A dermoscopic image of a skin lesion.
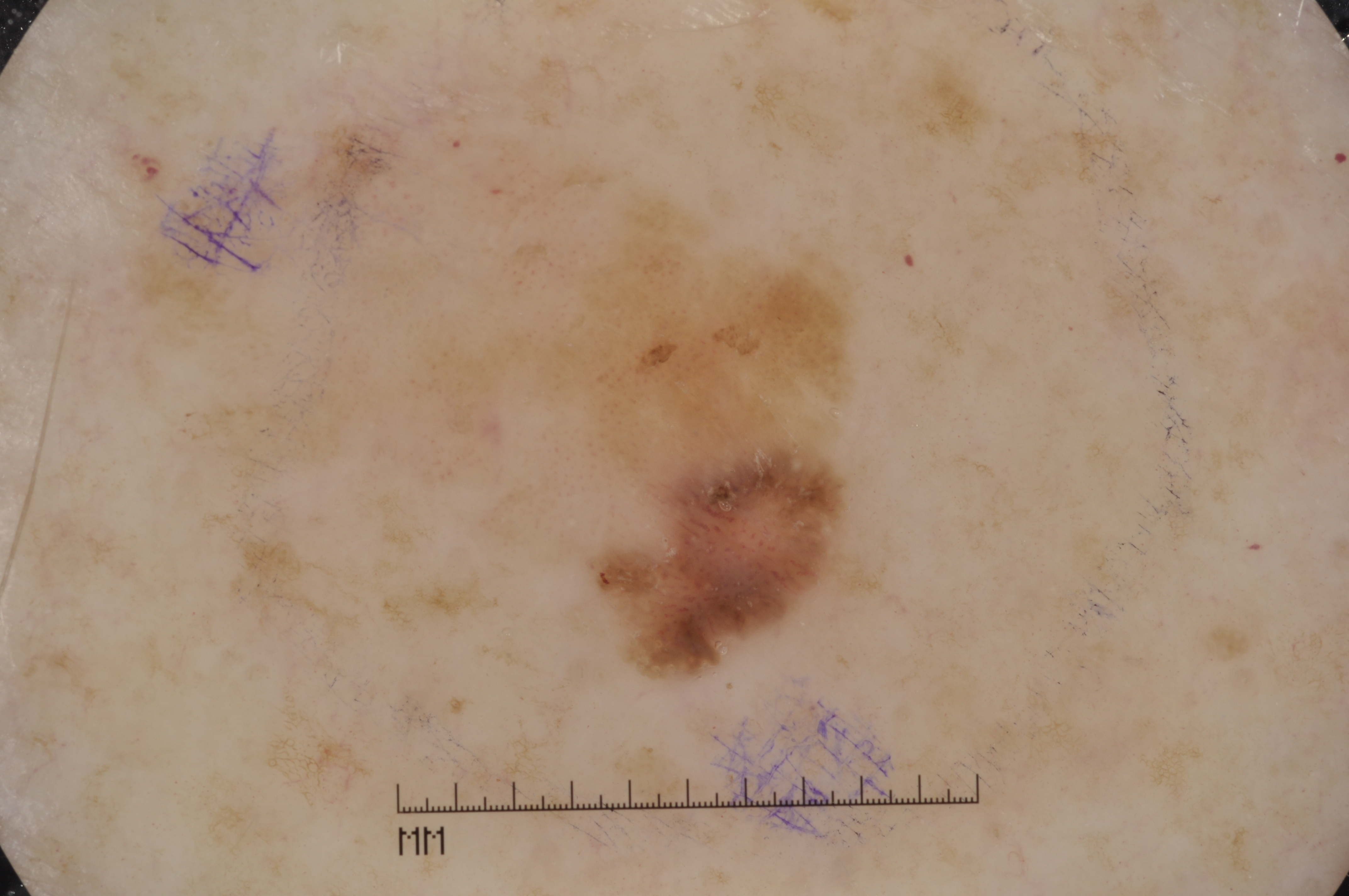The dermoscopic pattern shows negative network, pigment network, and milia-like cysts, with no streaks. The lesion occupies roughly 19% of the field. Lesion location: x1=180, y1=83, x2=907, y2=688. Expert review diagnosed this as a seborrheic keratosis.